The lesion is described as flat and raised or bumpy · the patient reported no systemic symptoms · the lesion is associated with itching and bothersome appearance · this image was taken at an angle · the lesion involves the arm · the patient is 40–49, female · present for one to four weeks · self-categorized by the patient as a rash.
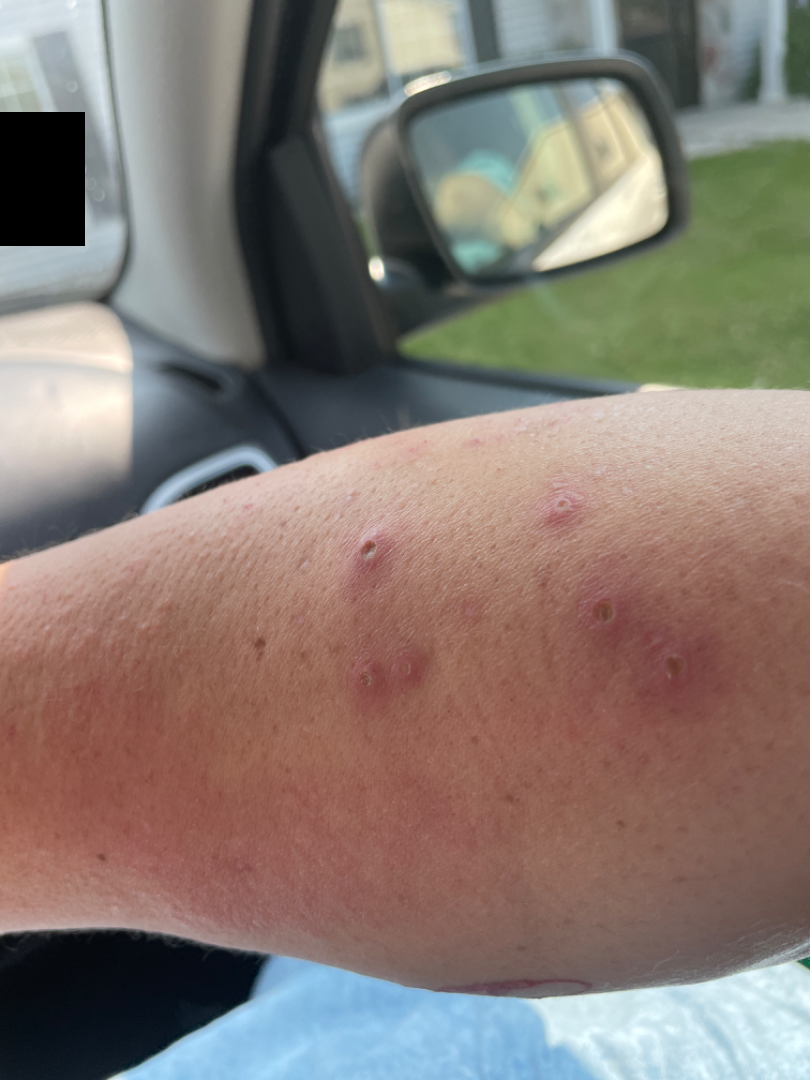<report>
  <assessment>indeterminate from the photograph</assessment>
</report>